A clinical close-up photograph of a skin lesion · a patient aged 14 — 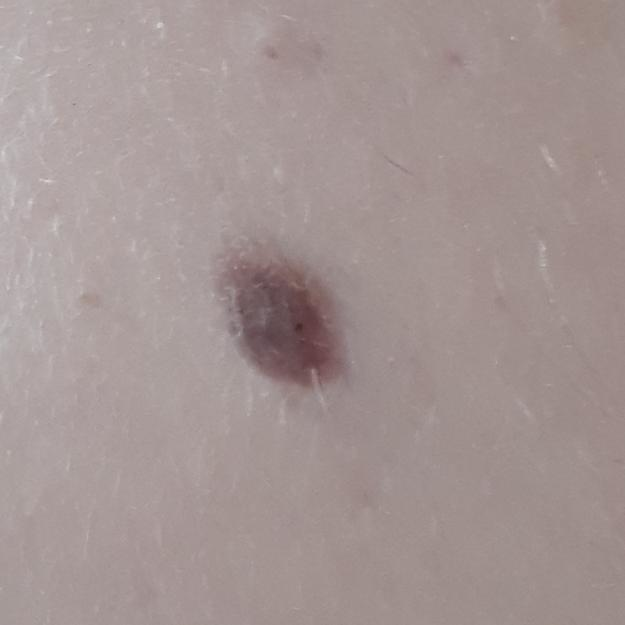Summary:
Located on the face.
Conclusion:
Clinically diagnosed as a nevus.